The photograph is a close-up of the affected area. The subject is 18–29, male. The head or neck, front of the torso, arm and back of the torso are involved — 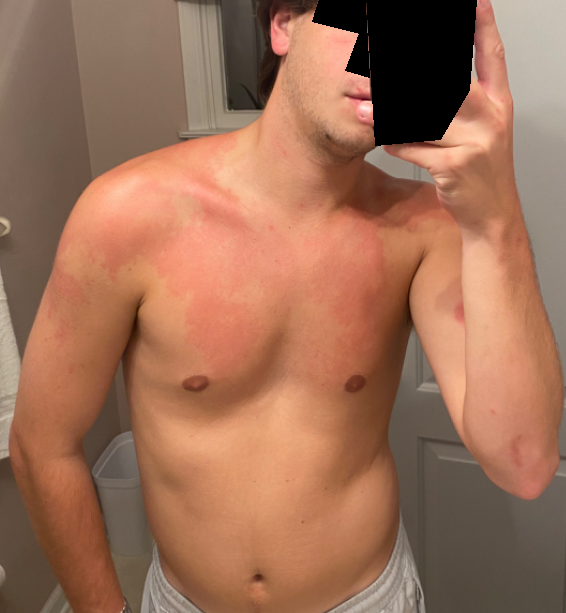assessment = unable to determine